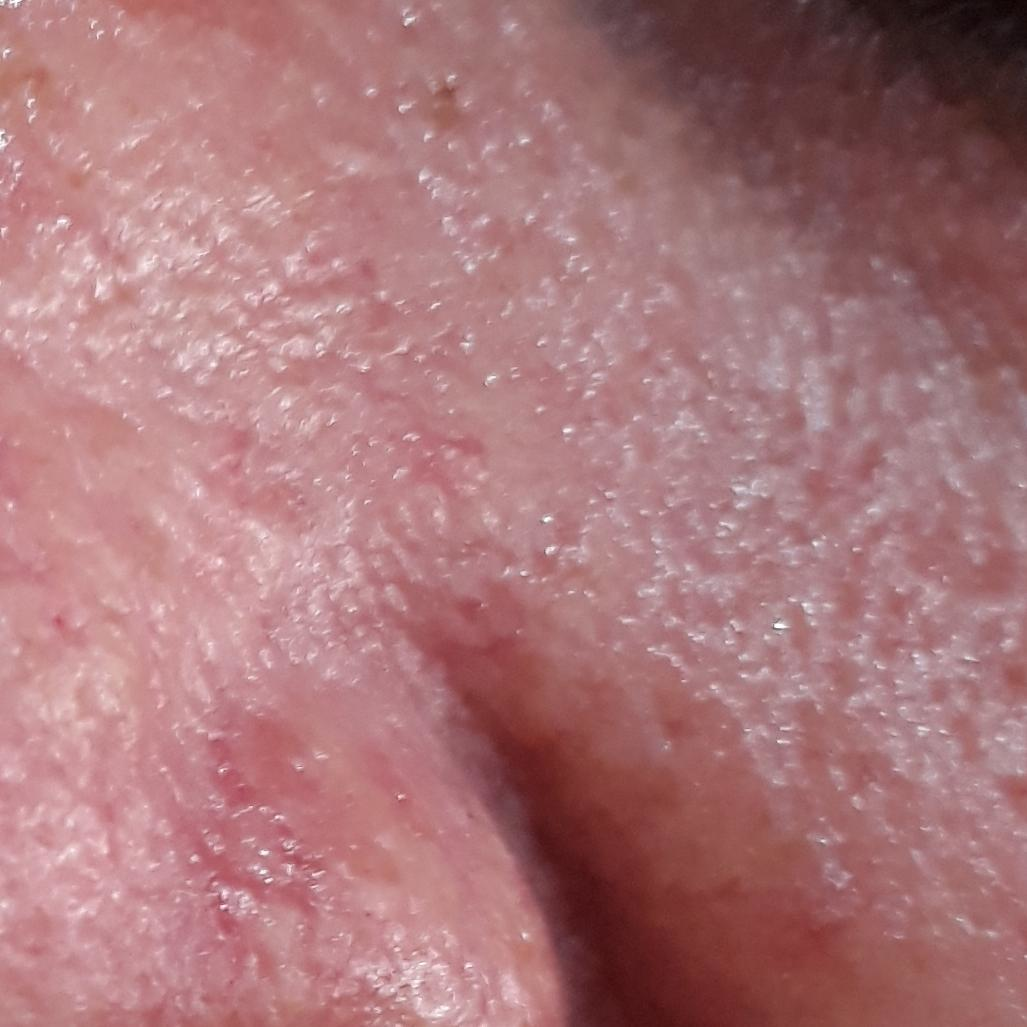A patient 50 years of age. A clinical photo of a skin lesion taken with a smartphone. Located on the nose. The clinical impression was an actinic keratosis.